A dermoscopy image of a single skin lesion.
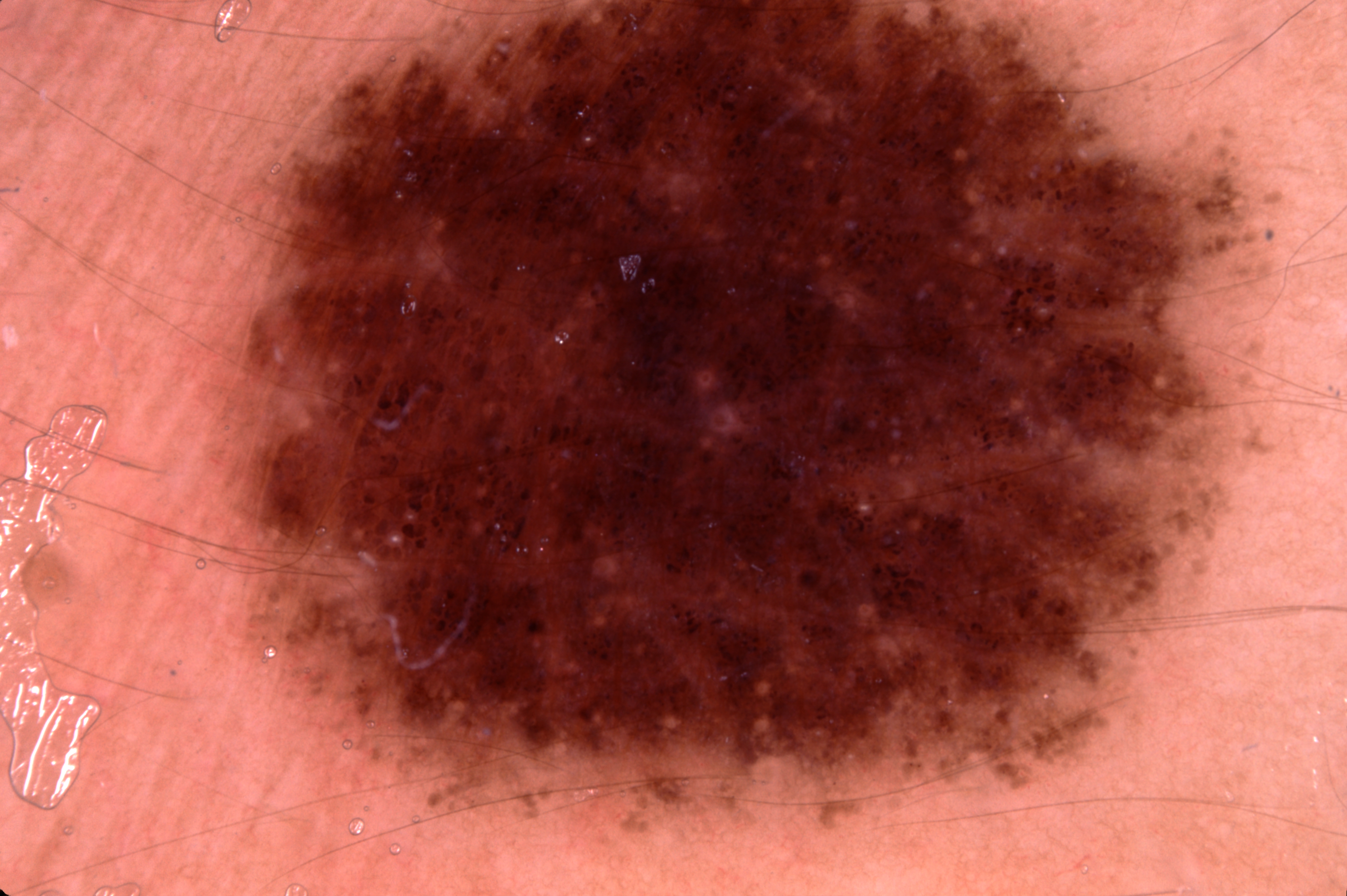The lesion is clipped by the edge of the image.
The lesion covers approximately 58% of the dermoscopic field.
As (left, top, right, bottom), the visible lesion spans 186 0 1257 833.
The dermoscopic pattern shows no streaks, pigment network, negative network, or milia-like cysts.
Expert review diagnosed this as a melanocytic nevus, a benign lesion.